A dermoscopic photograph of a skin lesion: 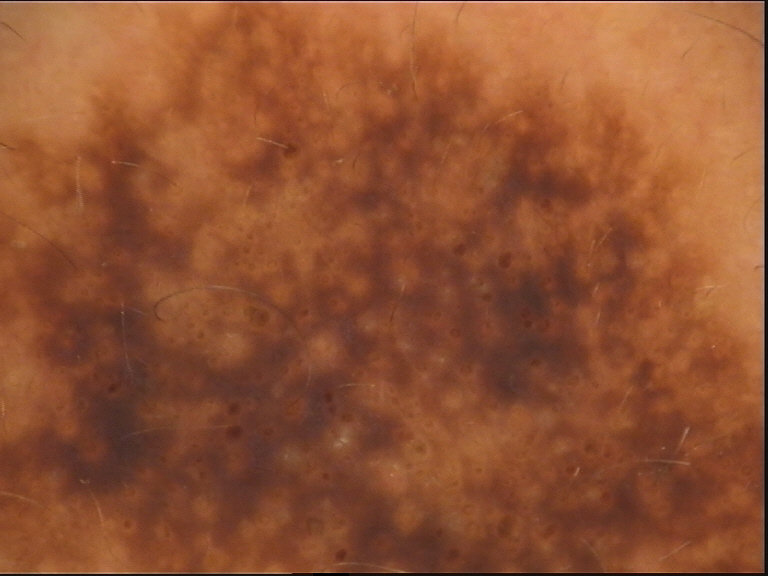Classified as a keratinocytic lesion — a seborrheic keratosis.